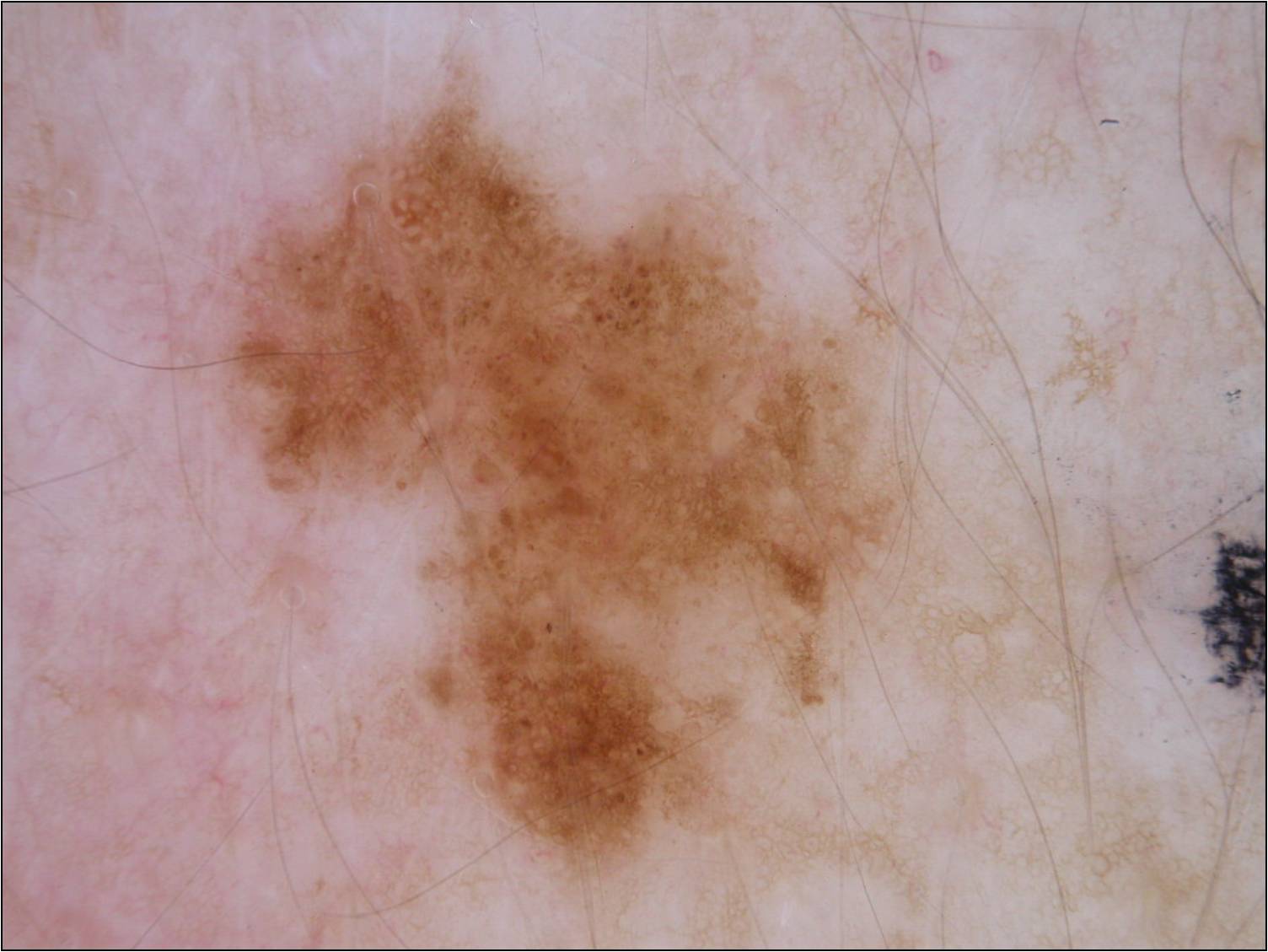A female patient aged approximately 55.
A dermatoscopic image of a skin lesion.
Dermoscopy demonstrates globules and pigment network, with no milia-like cysts, negative network, or streaks.
The lesion covers approximately 25% of the dermoscopic field.
With coordinates (x1, y1, x2, y2), the lesion is bounded by bbox=[218, 97, 912, 884].
The lesion was assessed as a melanocytic nevus.